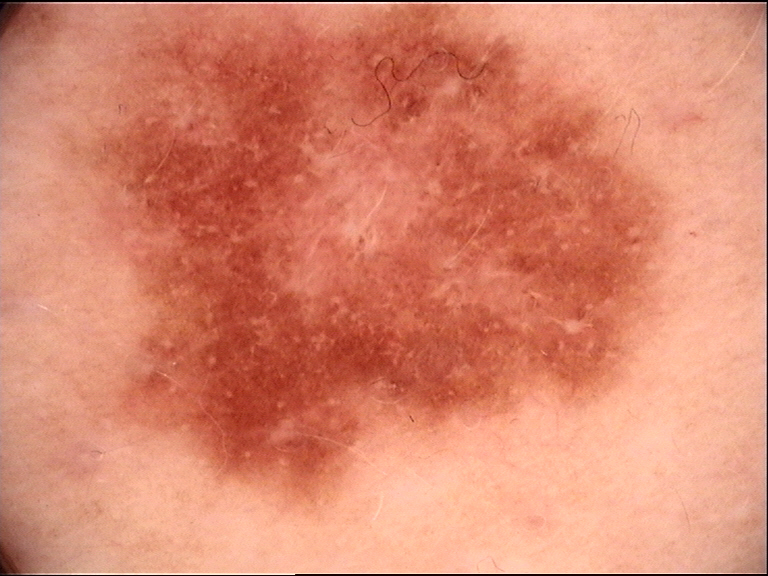{
  "diagnosis": {
    "name": "dysplastic junctional nevus",
    "code": "jd",
    "malignancy": "benign",
    "super_class": "melanocytic",
    "confirmation": "expert consensus"
  }
}